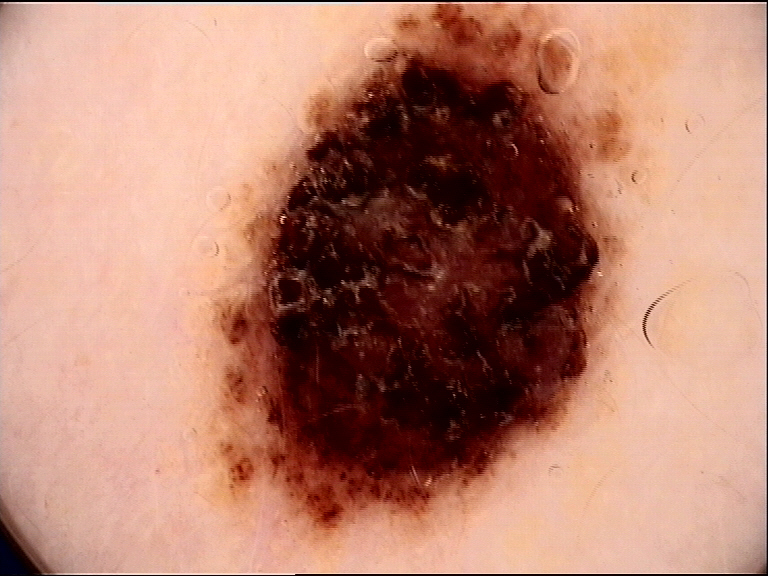Q: What is the imaging modality?
A: dermatoscopy
Q: What is this lesion?
A: dysplastic compound nevus (expert consensus)